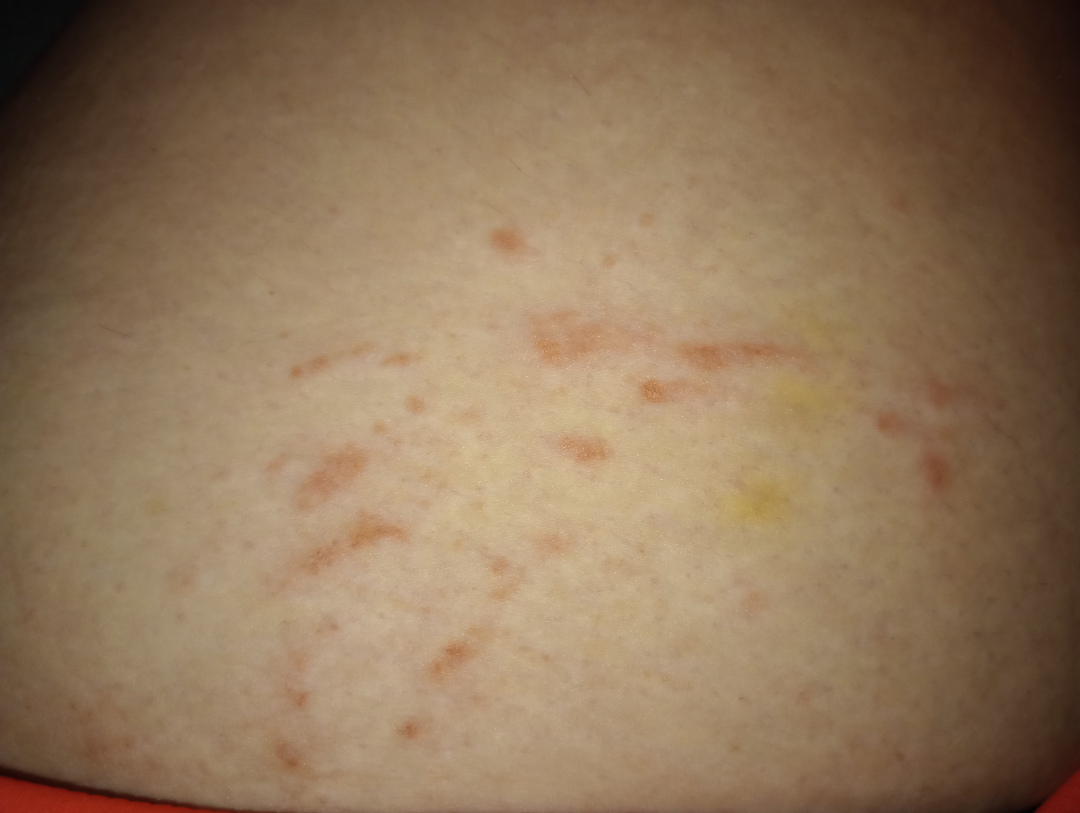Q: Patient's own categorization?
A: a rash
Q: When did this start?
A: one to four weeks
Q: Reported symptoms?
A: itching
Q: What is the framing?
A: close-up
Q: Anatomic location?
A: leg
Q: Texture?
A: raised or bumpy
Q: What is the dermatologist's impression?
A: Eczema (50%); Allergic Contact Dermatitis (50%)